The contributor reports the lesion is raised or bumpy; the contributor reports the condition has been present for less than one week; self-categorized by the patient as a rash; the leg is involved; the photograph was taken at an angle; male subject, age 18–29.
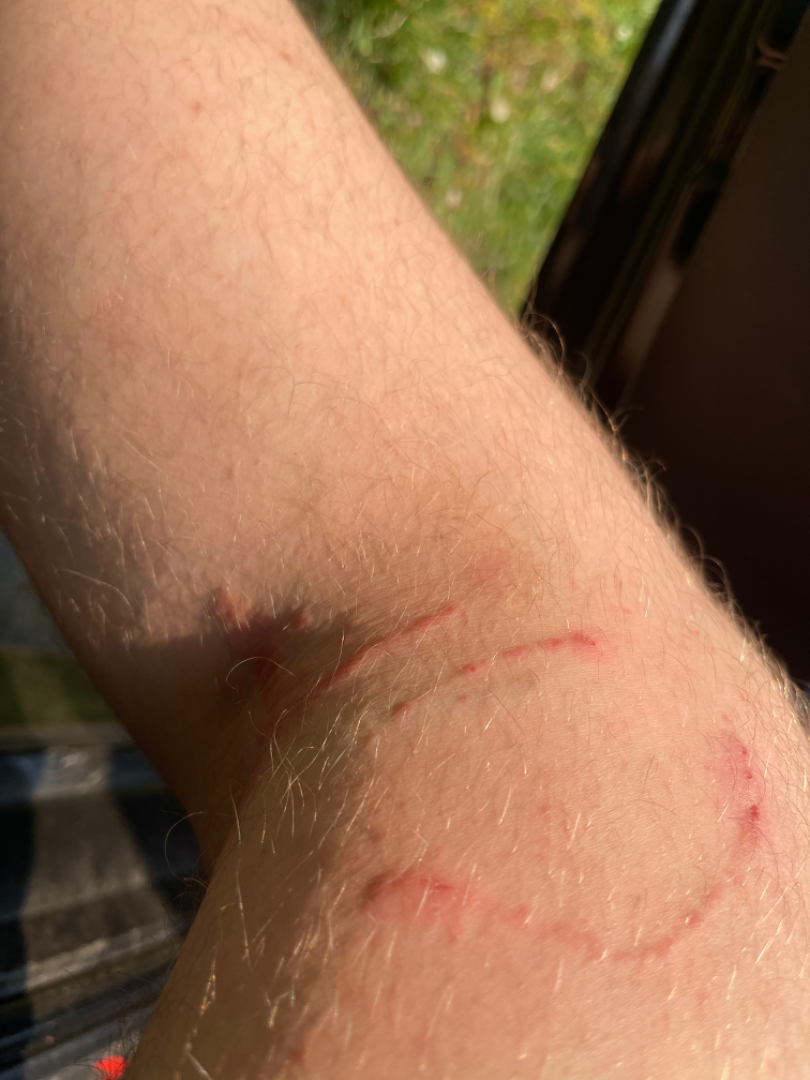differential diagnosis = reviewed remotely by one dermatologist: Tinea and Erythema annulare centrifugum were each considered, in no particular order.